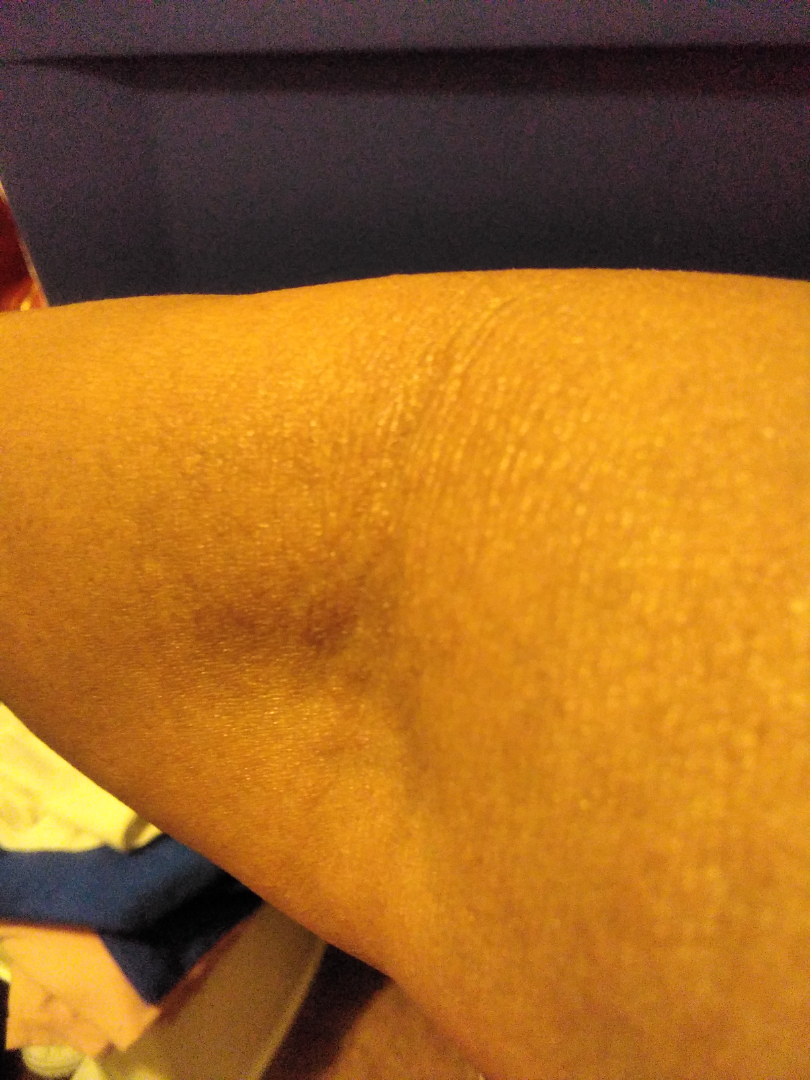No discernible pathology was noted by the reviewing dermatologist. Located on the head or neck. The lesion is described as flat. The contributor is a female aged 50–59. This is a close-up image. The patient described the issue as a rash. Fitzpatrick IV; human graders estimated 3 on the MST. Present for one to four weeks. Symptoms reported: itching.